A clinical photograph showing a skin lesion — 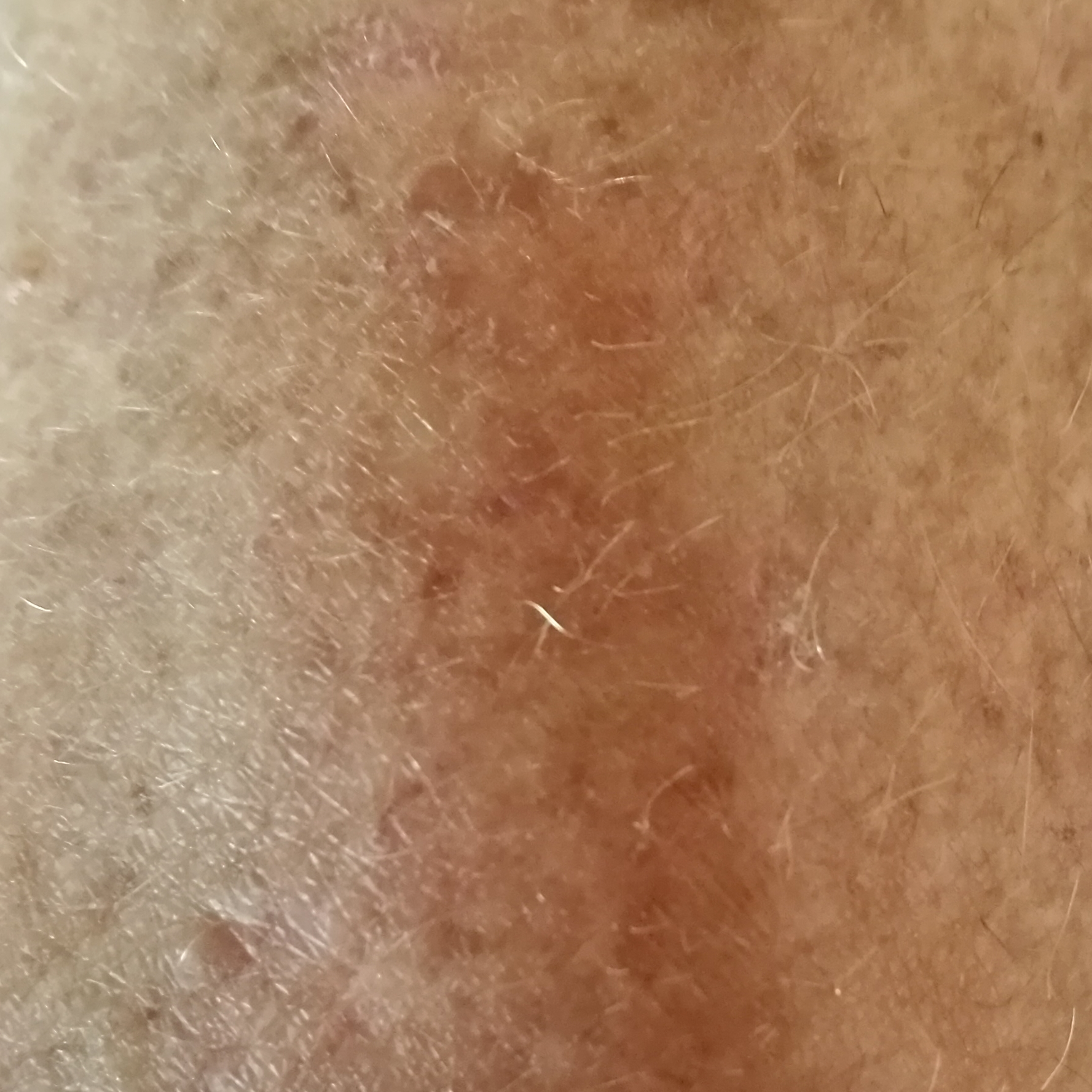| feature | finding |
|---|---|
| region | a forearm |
| patient-reported symptoms | itching |
| impression | actinic keratosis (clinical consensus) |